The photo was captured at an angle · the lesion involves the palm and arm — 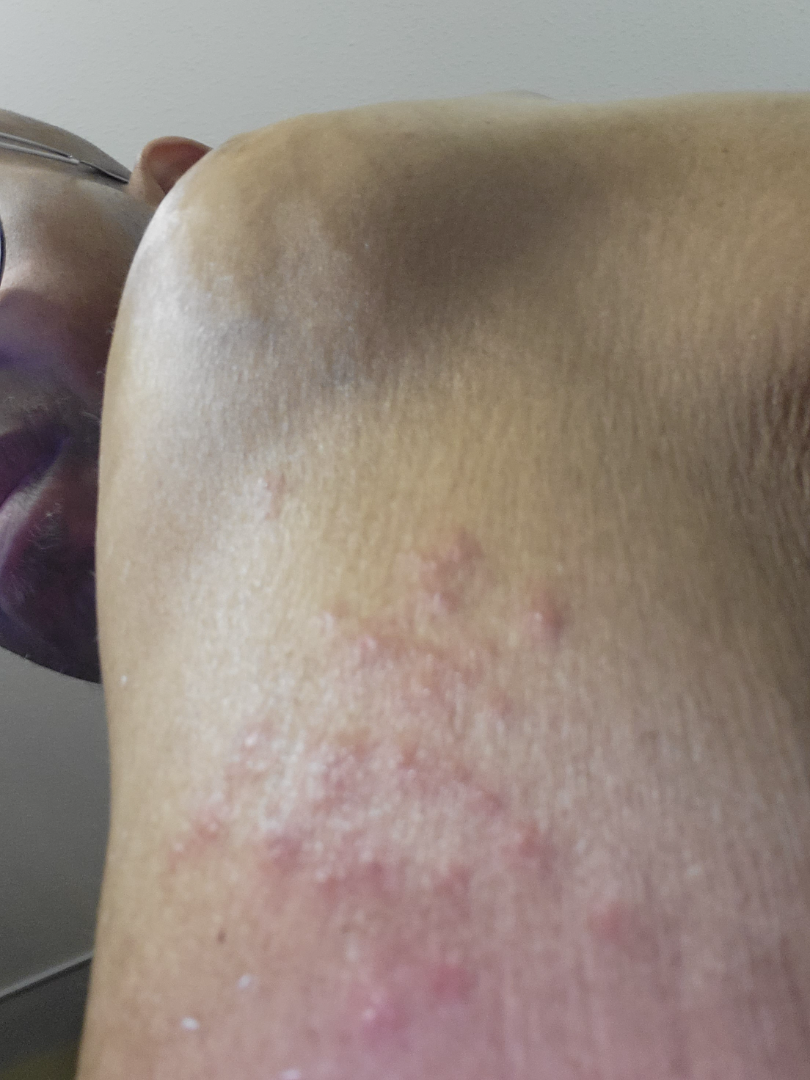The image was not sufficient for the reviewer to characterize the skin condition.